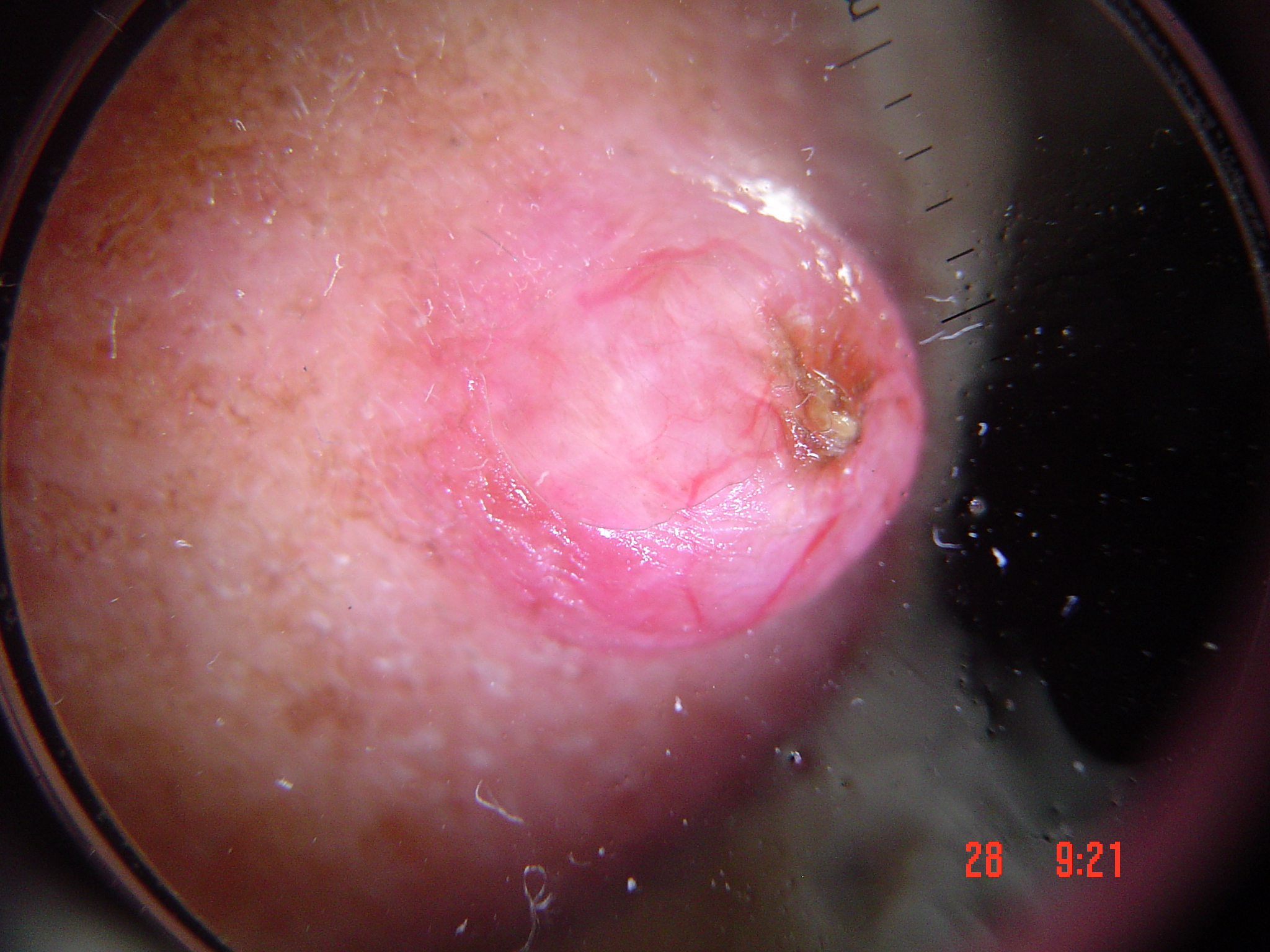Findings:
* modality — dermoscopy
* pathology — basal cell carcinoma (biopsy-proven)